The patient described the issue as a rash · the photograph is a close-up of the affected area · the affected area is the top or side of the foot, head or neck, back of the torso, leg, front of the torso and back of the hand · reported duration is less than one week · the lesion is described as flat: 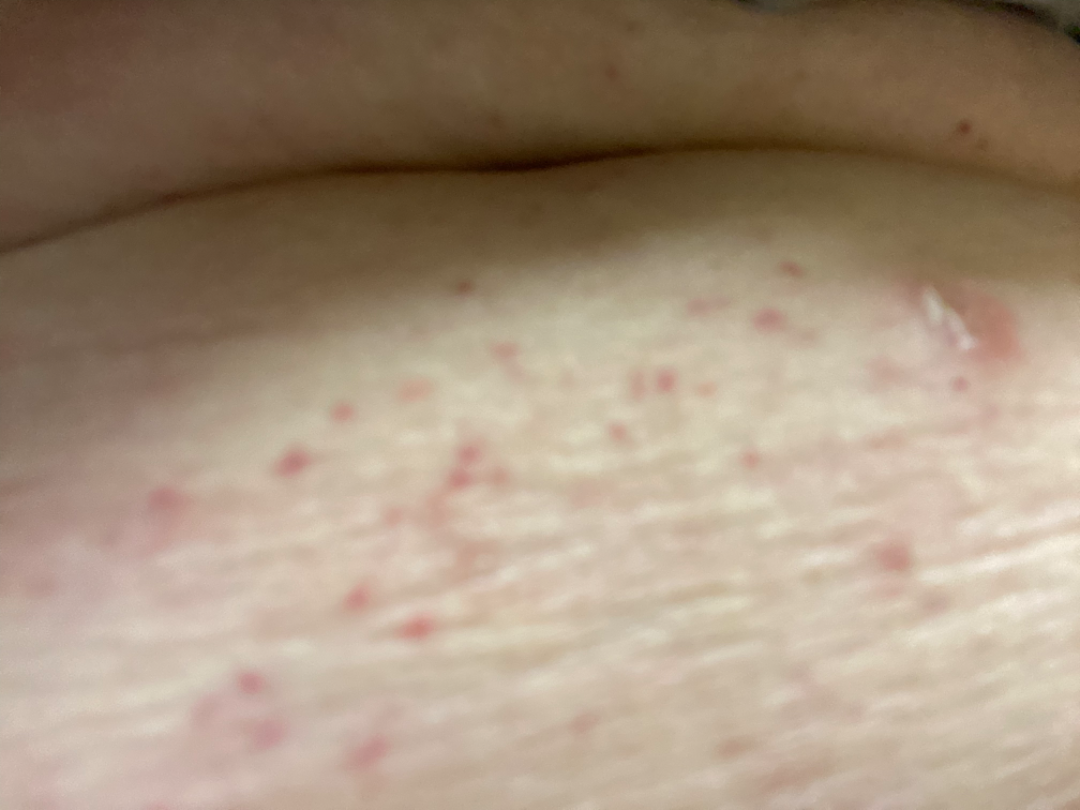Assessment: On photographic review: the differential is split between Scabies, Eczema and Hypersensitivity.